This is a close-up image: 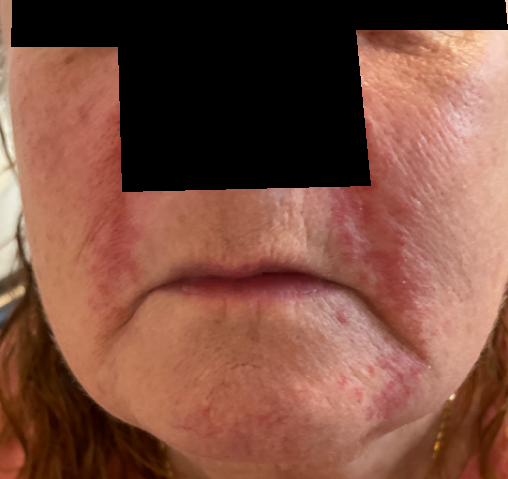Q: What conditions are considered?
A: Perioral Dermatitis (favored); Rosacea (considered)